Dermoscopy of a skin lesion:
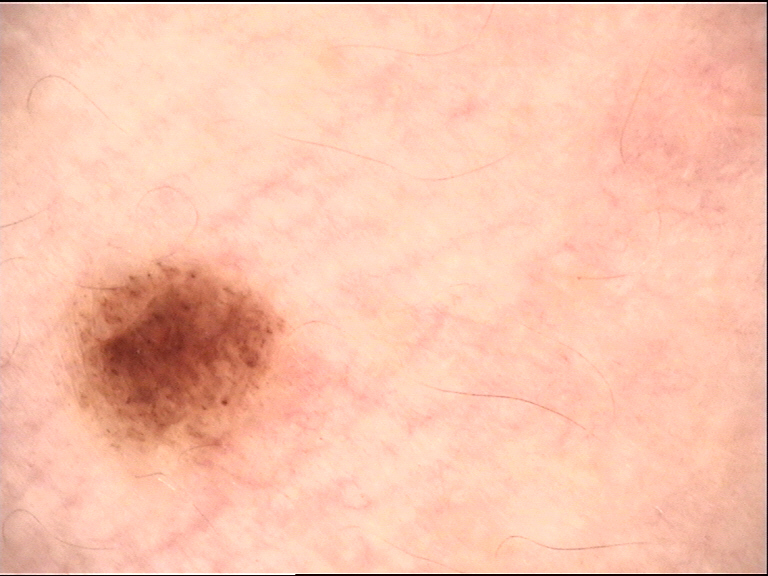Case:
This is a banal lesion.
Conclusion:
The diagnosis was a compound nevus.